The photograph is a close-up of the affected area; the affected area is the arm — 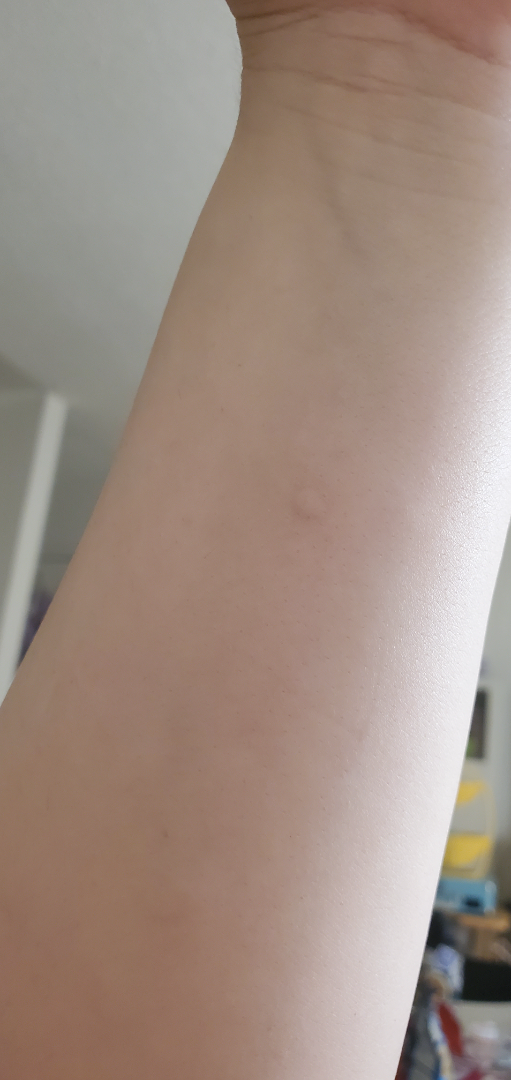Q: What was the assessment?
A: unable to determine